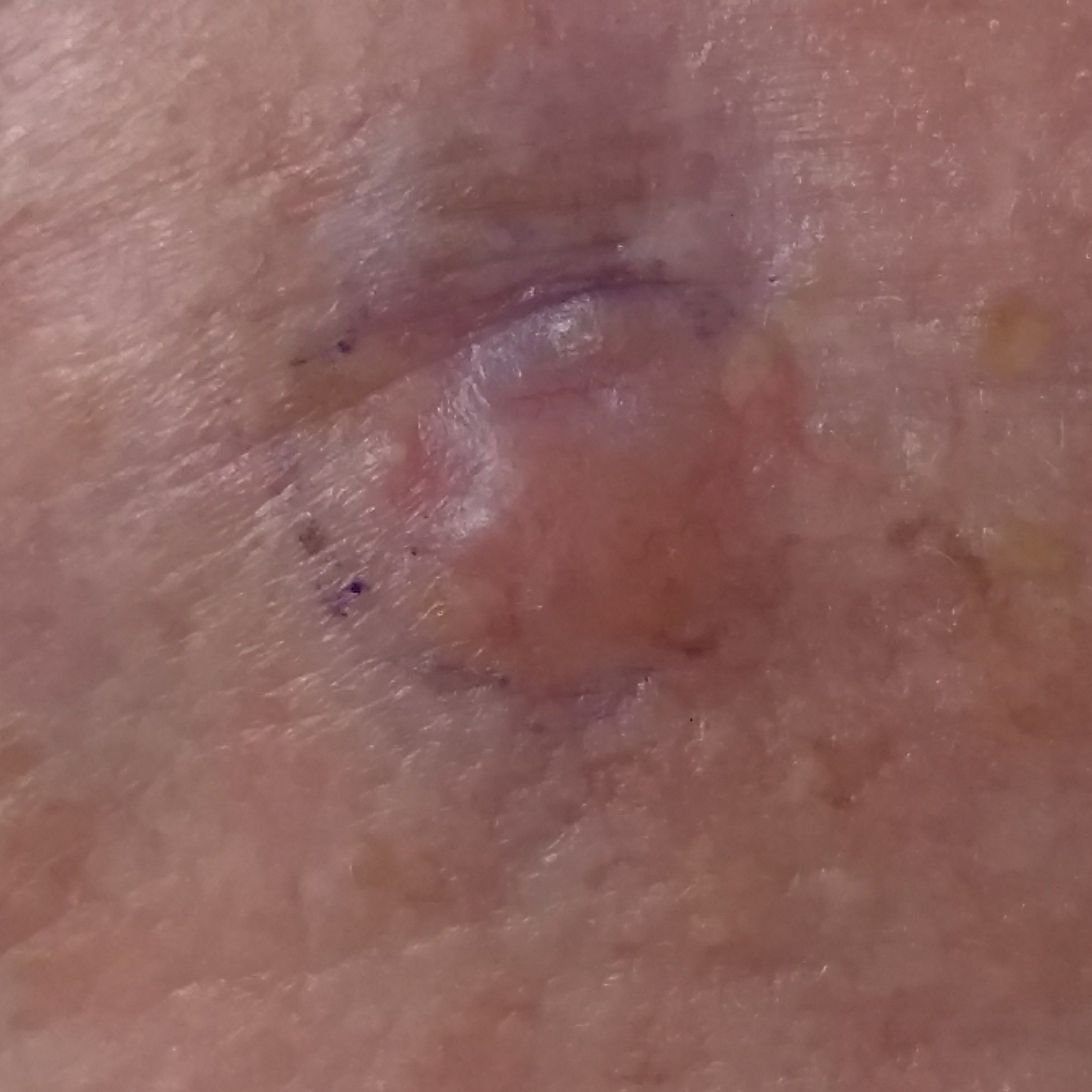skin phototype: I
subject: male, in their 70s
image: clinical photograph
exposure history: alcohol use, prior malignancy (patient or family)
anatomic site: the face
lesion size: approx. 10 × 6 mm
symptoms: elevation, growth
diagnosis: basal cell carcinoma (biopsy-proven)